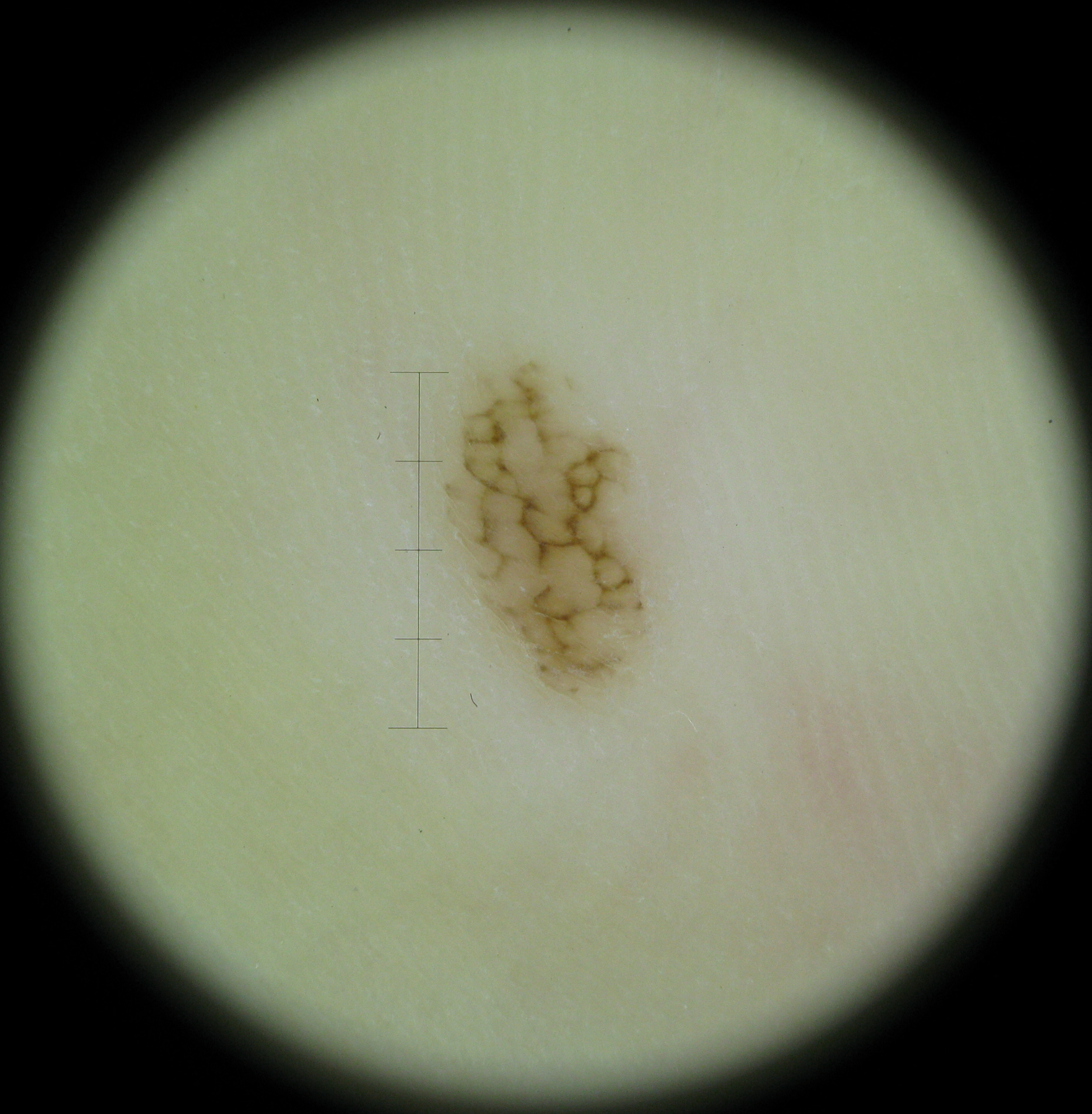Case:
A dermoscopy image of a single skin lesion.
Conclusion:
Consistent with a banal lesion — an acral compound nevus.